A clinical close-up photograph of a skin lesion — 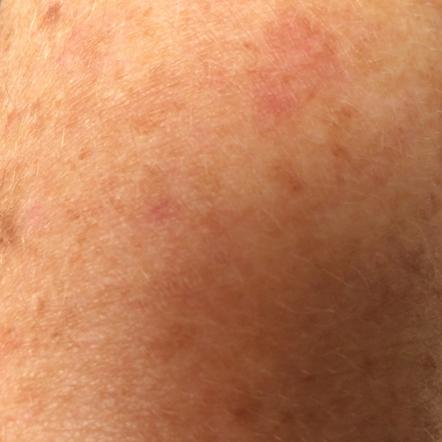Findings: No symptoms reported. Conclusion: The consensus clinical diagnosis was an actinic keratosis.